A dermoscopic photograph of a skin lesion.
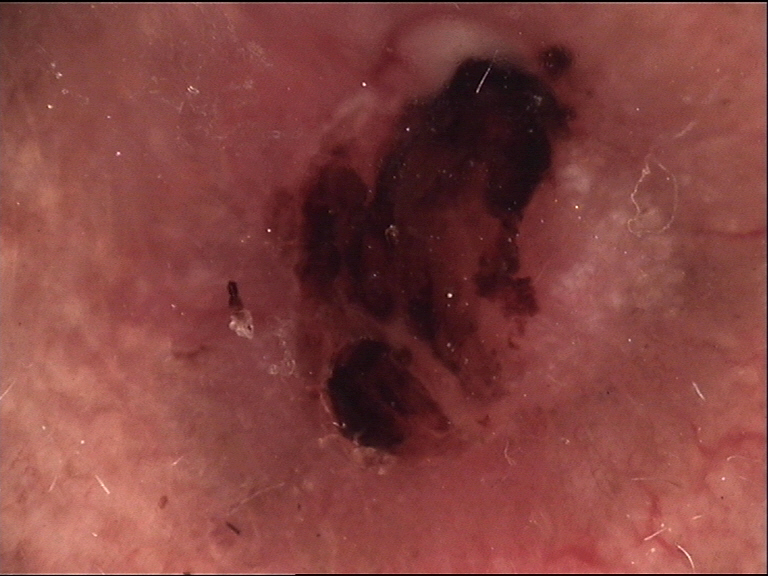| field | value |
|---|---|
| label | basal cell carcinoma (biopsy-proven) |